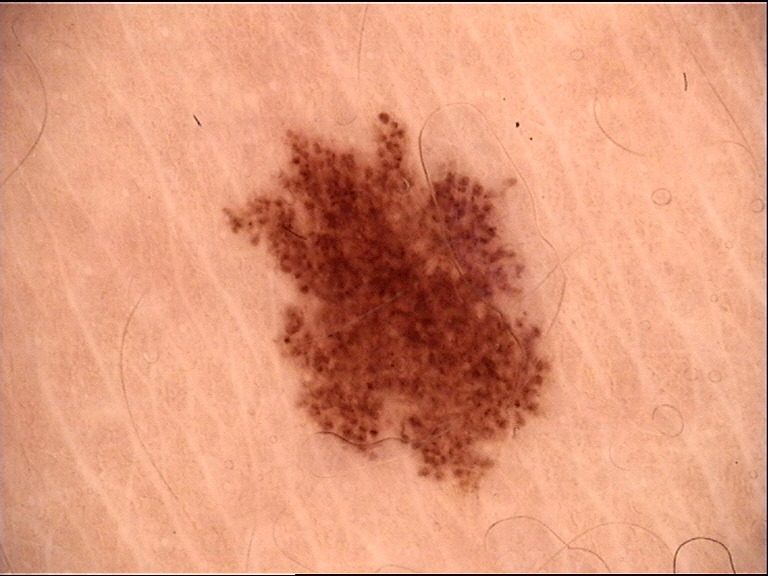Classified as a dysplastic junctional nevus.